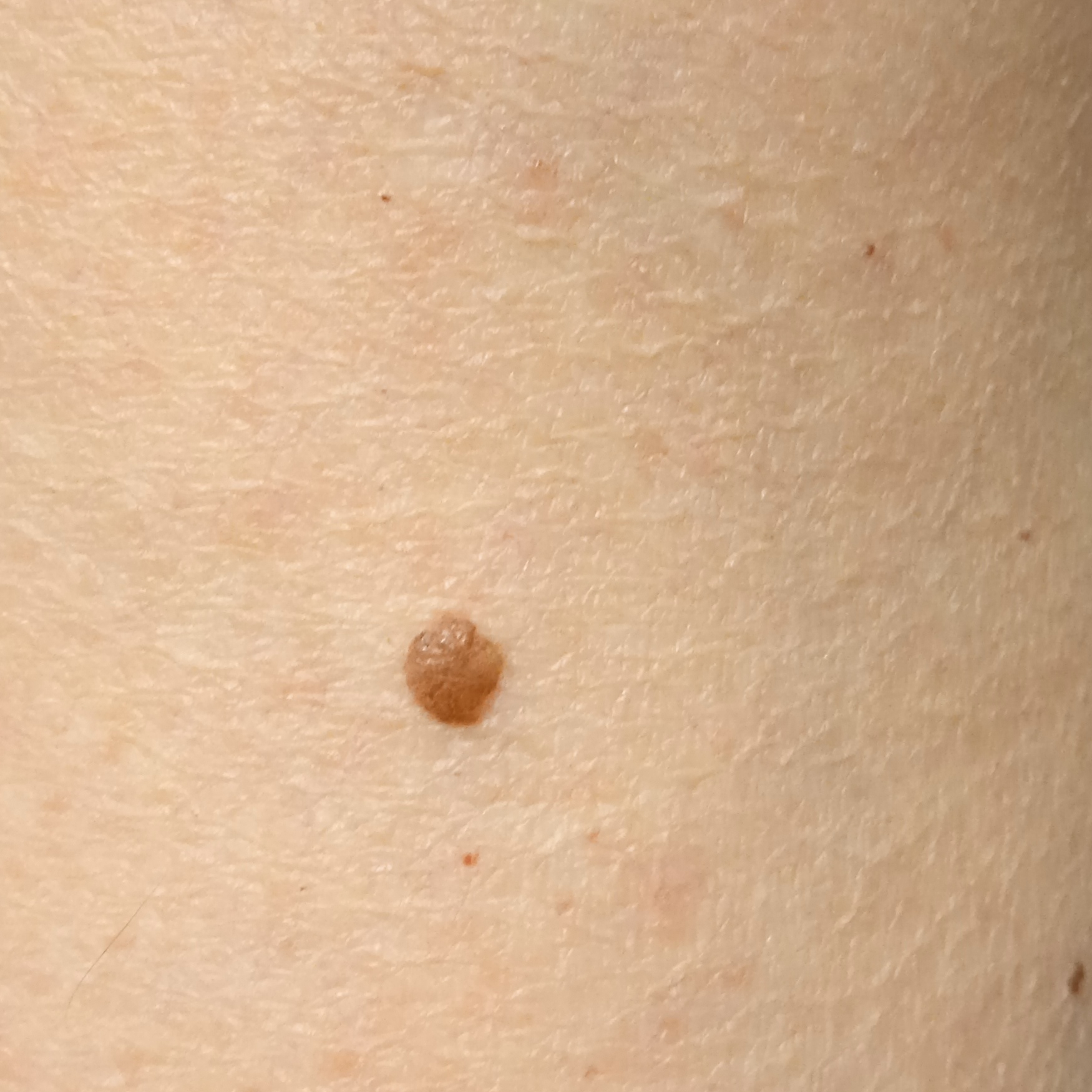On a questionnaire the patient reported a personal history of skin cancer, a family history of skin cancer, and immunosuppression. The patient says their skin reddens painfully with sun exposure. A macroscopic clinical photograph of a skin lesion. Acquired for a research image collection, with no referral diagnosis. Located on an arm. Measuring roughly 3 mm. The dermatologists' assessment was a melanocytic nevus.